An image taken at a distance · the lesion involves the arm, head or neck, leg, front of the torso, back of the torso and palm:
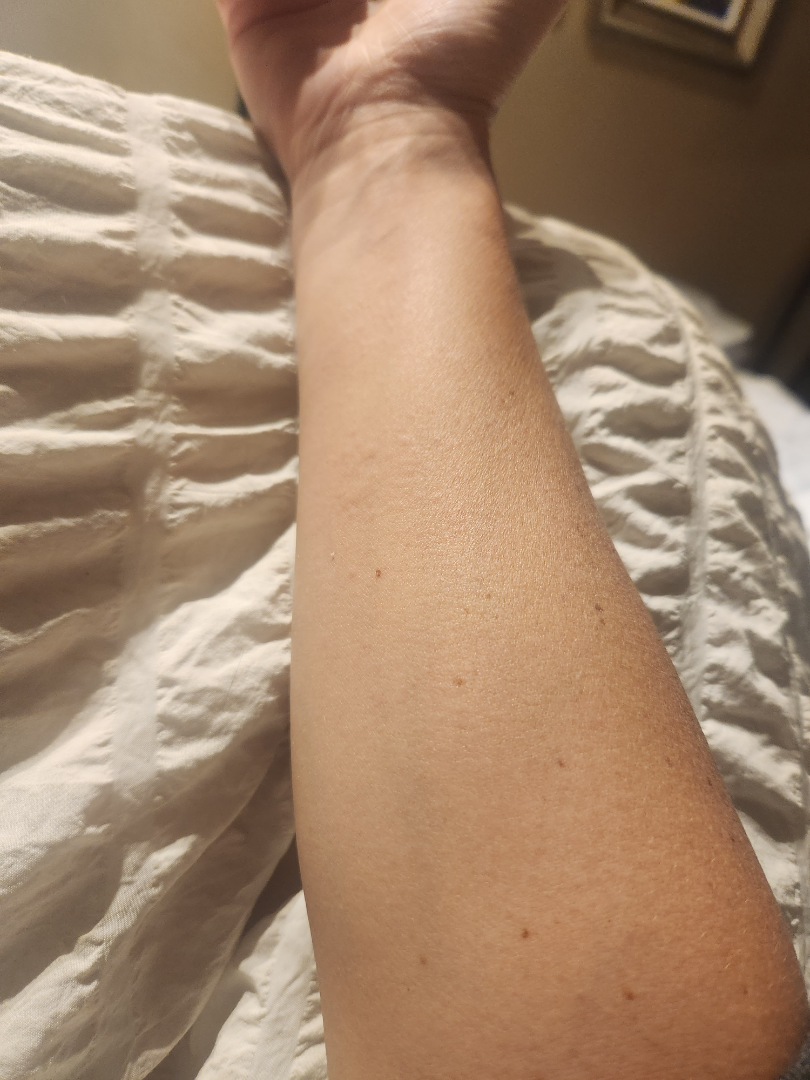Q: How does the lesion feel?
A: flat and raised or bumpy
Q: What symptoms does the patient report?
A: pain, burning and itching
Q: How does the patient describe it?
A: a rash
Q: When did this start?
A: one to three months
Q: What conditions are considered?
A: favoring Urticaria; less probable is Eczema